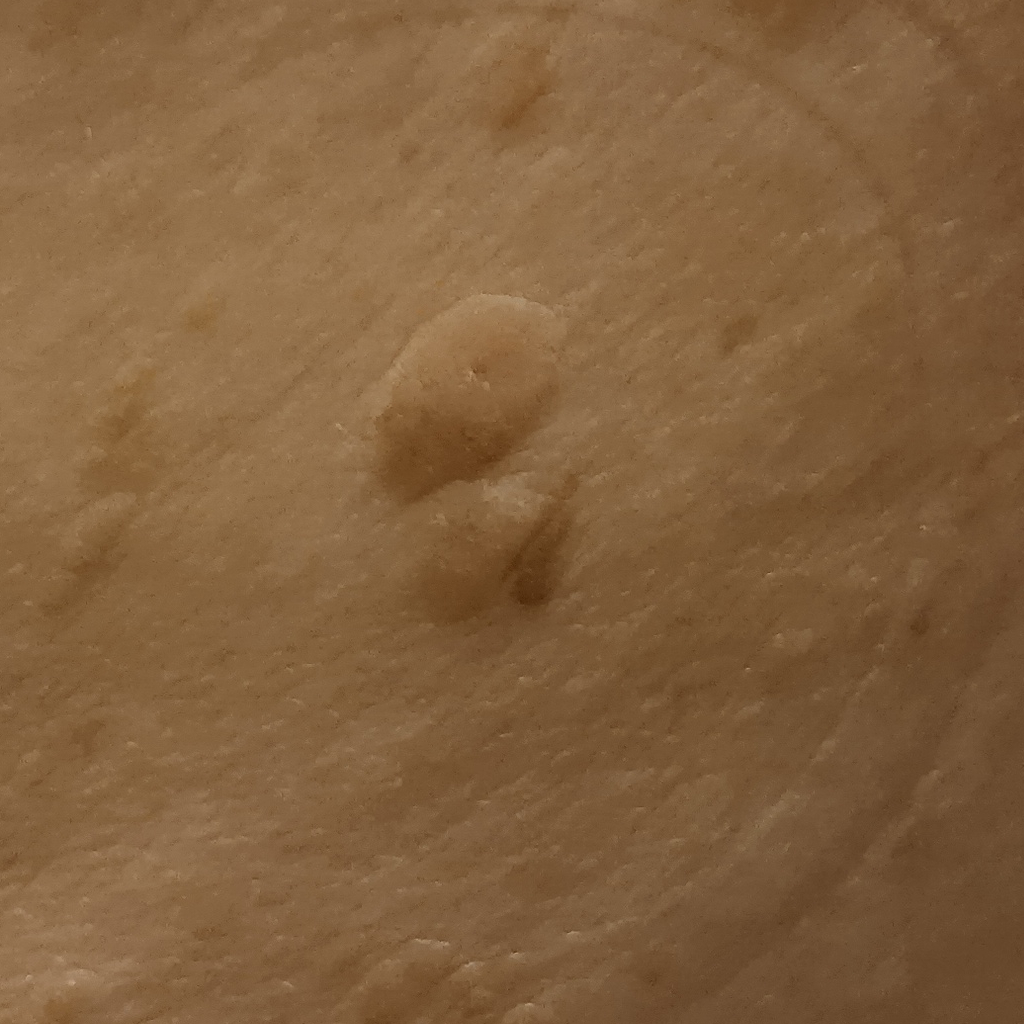<lesion>
  <diagnosis>
    <name>seborrheic keratosis</name>
    <malignancy>benign</malignancy>
  </diagnosis>
</lesion>